The contributor is 18–29, female; a close-up photograph; the affected area is the arm: 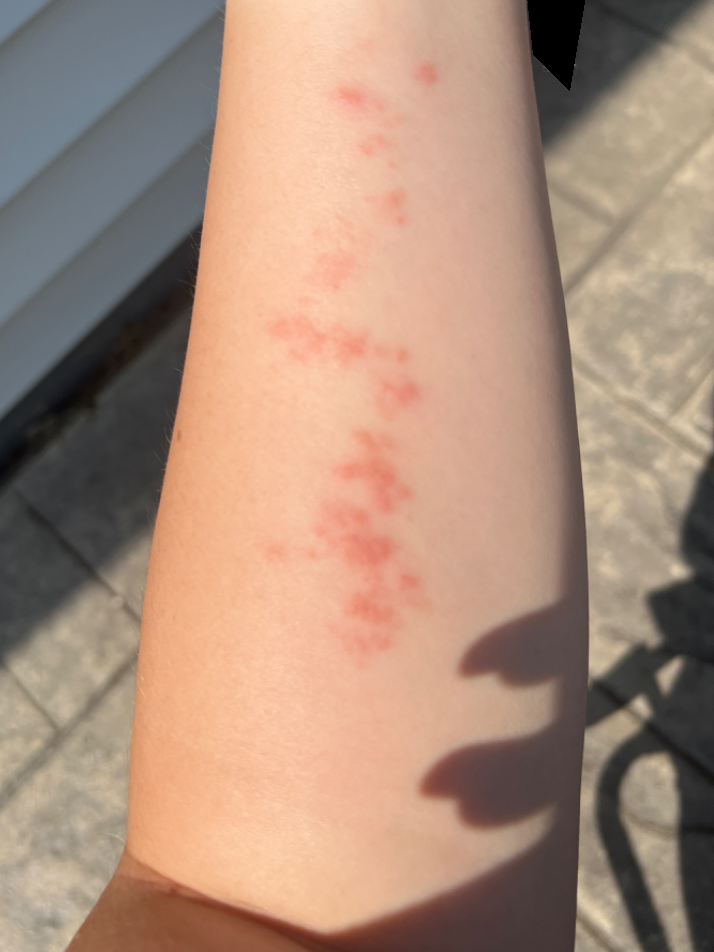Texture is reported as raised or bumpy.
Self-categorized by the patient as a rash.
The reviewing dermatologist's impression was: Insect Bite (considered); Allergic Contact Dermatitis (considered); Herpes Zoster (remote).